A skin lesion imaged with a dermatoscope: 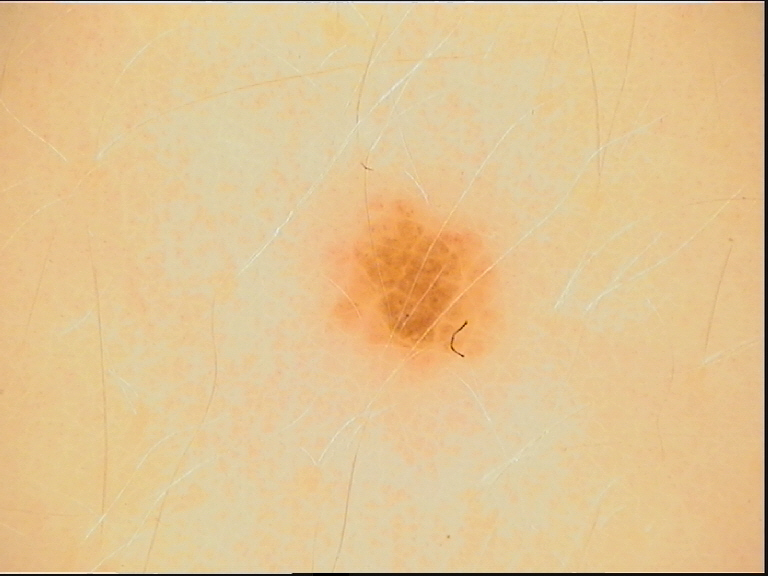classification = banal; assessment = junctional nevus (expert consensus).